The photograph is a close-up of the affected area · the affected area is the front of the torso — 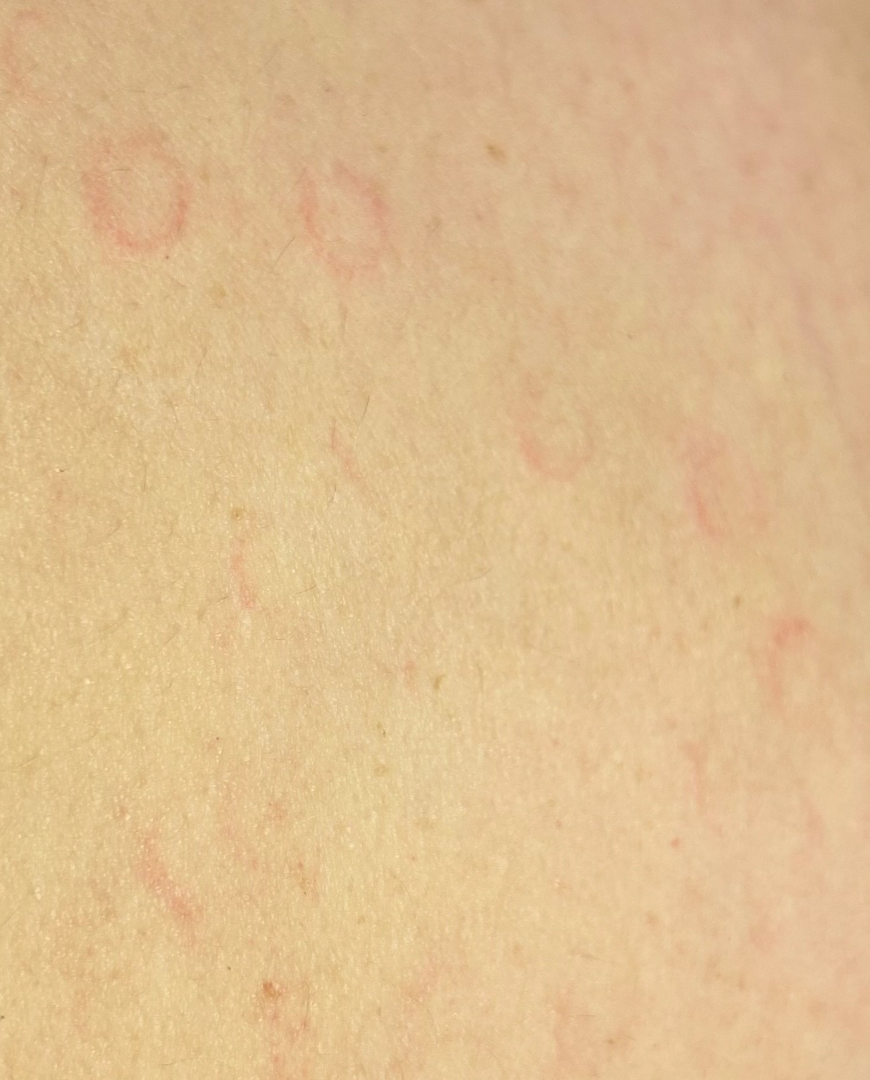Findings:
The case was difficult to assess from the available photograph.